History notes prior malignancy (patient or family) and prior skin cancer (patient or family) · a clinical photograph showing a skin lesion — 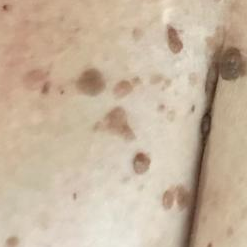The lesion is located on the chest.
The lesion is roughly 17 by 15 mm.
The patient describes that the lesion has grown and is elevated.
Diagnosed by dermatologist consensus as a benign skin lesion — a seborrheic keratosis.